A dermoscopic photograph of a skin lesion.
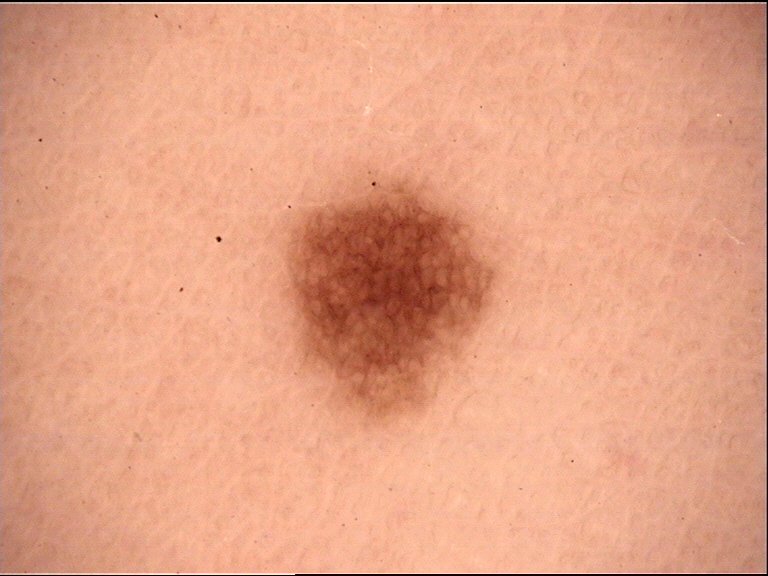This is a banal lesion. Diagnosed as a junctional nevus.